This is a dermoscopic photograph of a skin lesion:
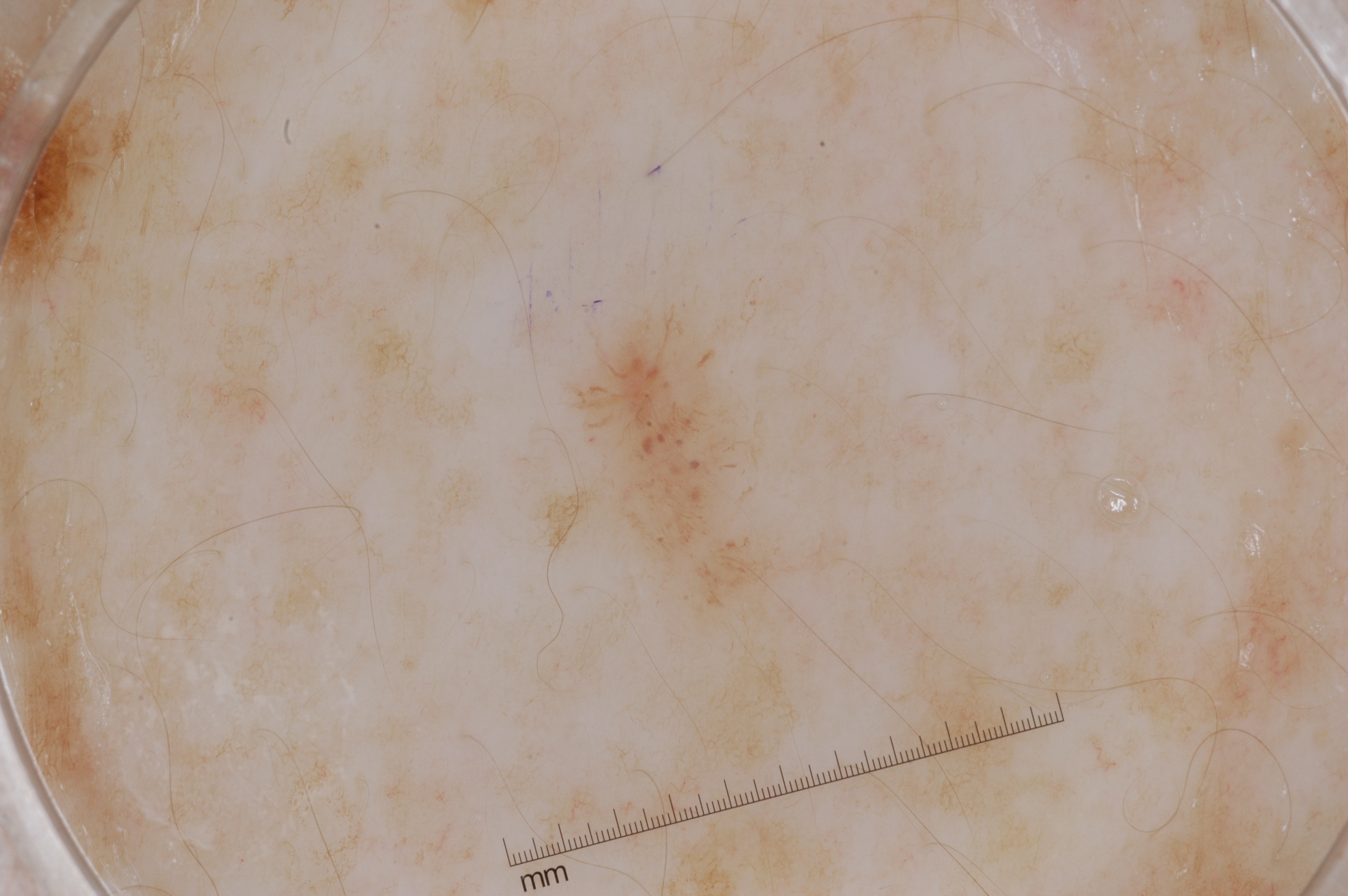The visible lesion spans left=579, top=315, right=737, bottom=546.
The dermoscopic pattern shows pigment network, with no streaks, negative network, or milia-like cysts.
Consistent with a melanocytic nevus, a benign skin lesion.